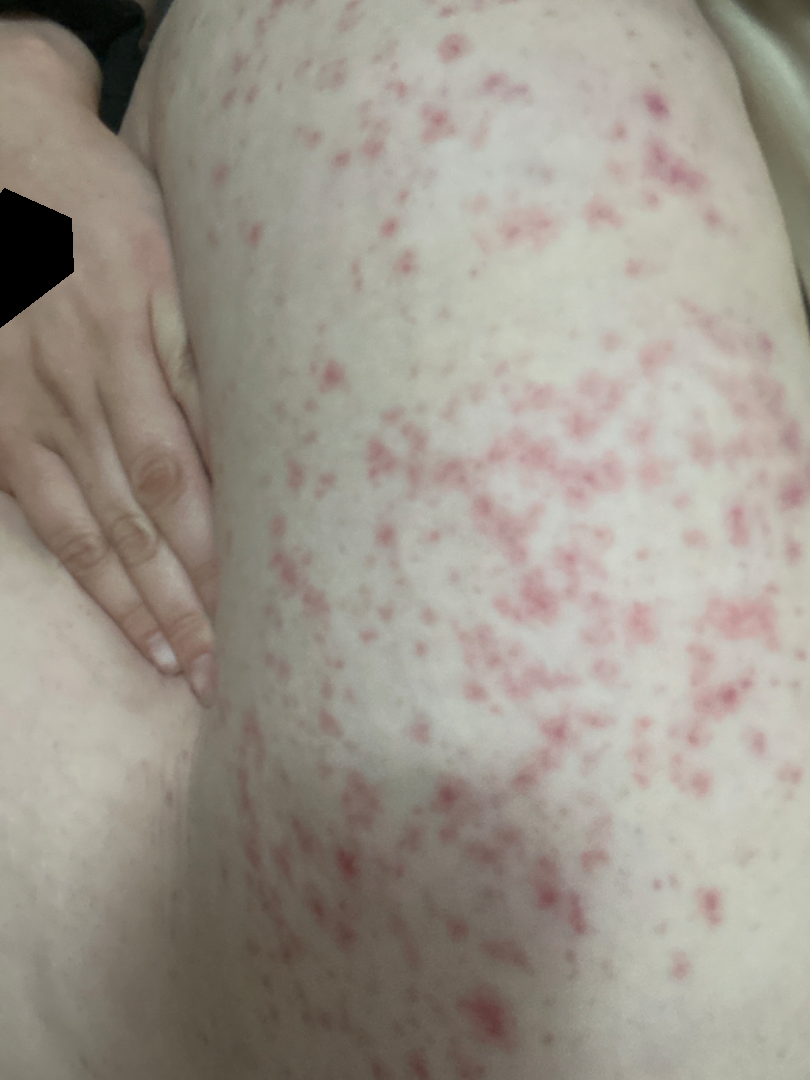Notes:
* assessment — indeterminate
* location — top or side of the foot, front of the torso and leg
* contributor — female, age 18–29
* framing — close-up